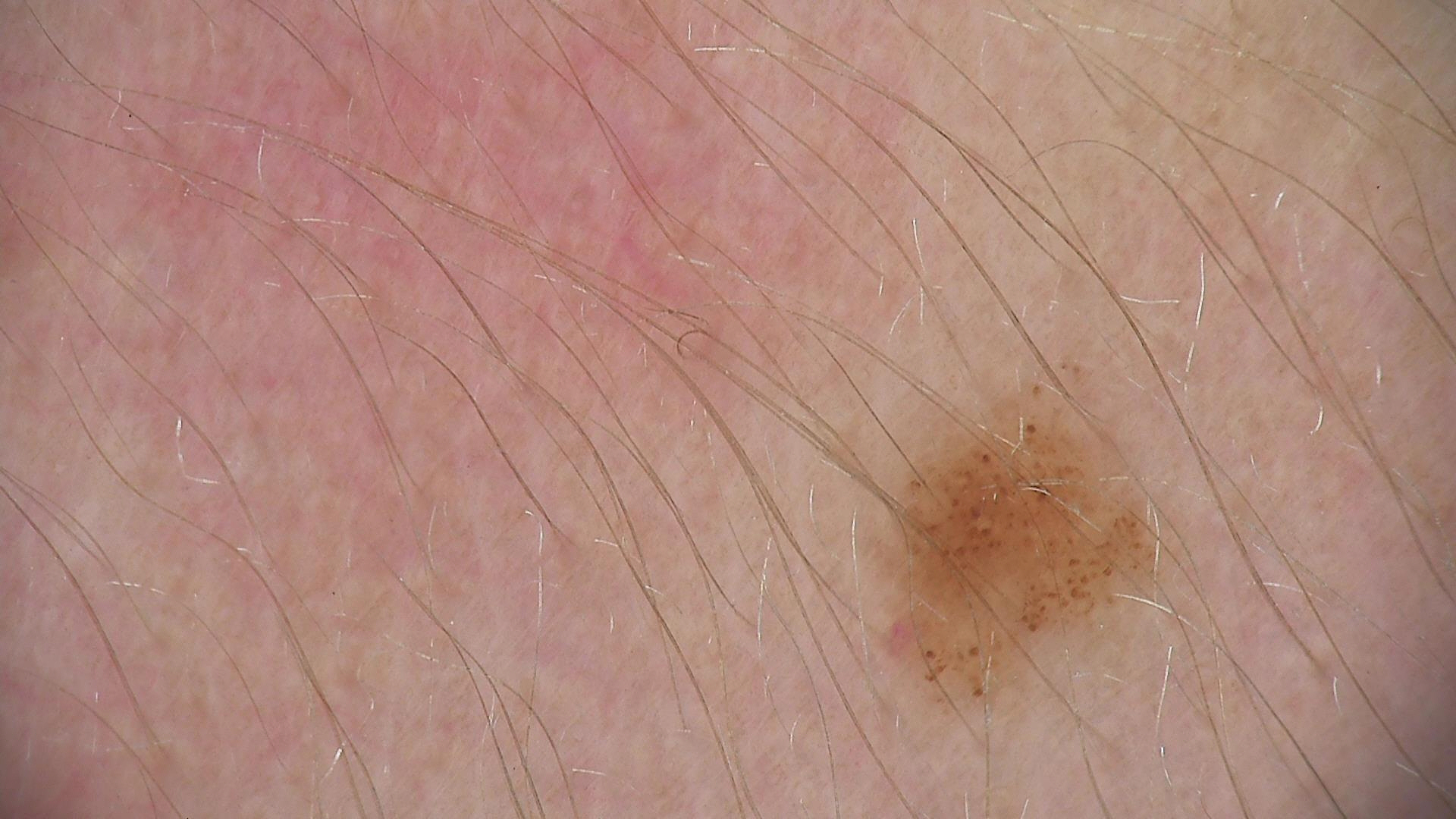A dermoscopic image of a skin lesion. Diagnosed as a benign lesion — a dysplastic junctional nevus.